The contributor notes the lesion is raised or bumpy. The contributor notes bothersome appearance. No associated systemic symptoms reported. The photograph was taken at an angle. Skin tone: Fitzpatrick skin type III; lay reviewers estimated 2 on the MST. The patient is a female aged 40–49. The head or neck is involved: 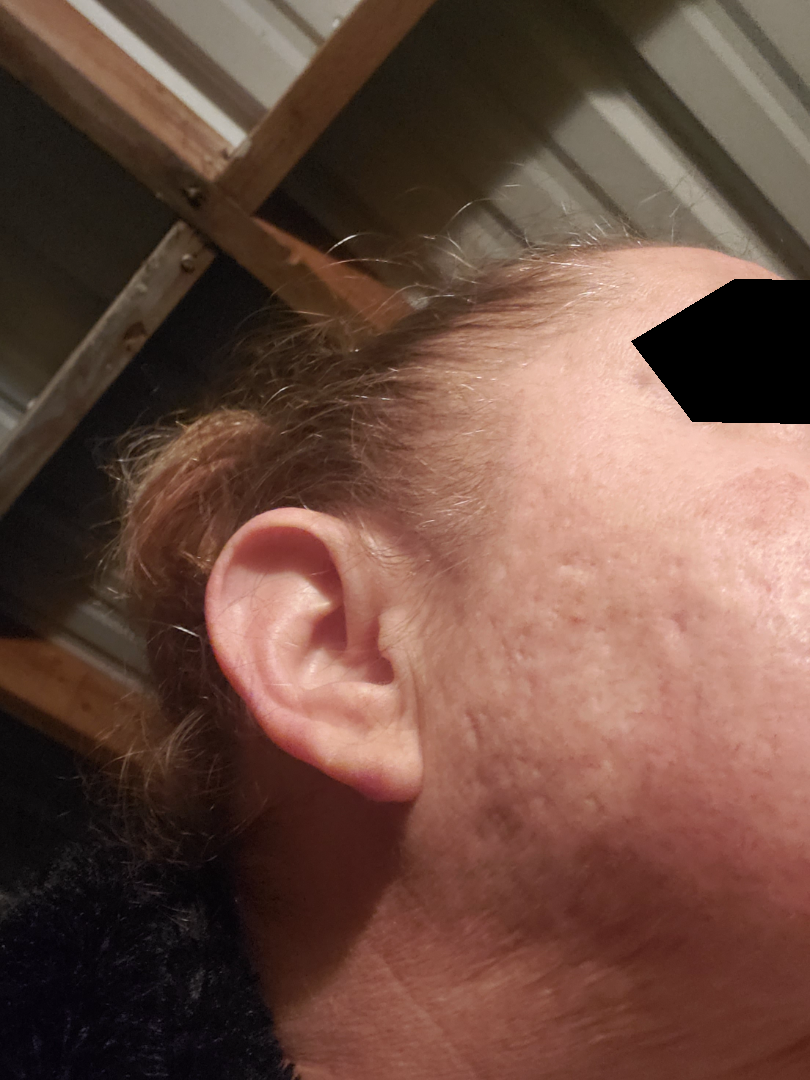Most consistent with Scar Condition.